Numerous moles by the patient's own estimate. Collected as part of a research study, without a referral diagnosis. A female subject aged 78. Dermoscopy of a skin lesion.
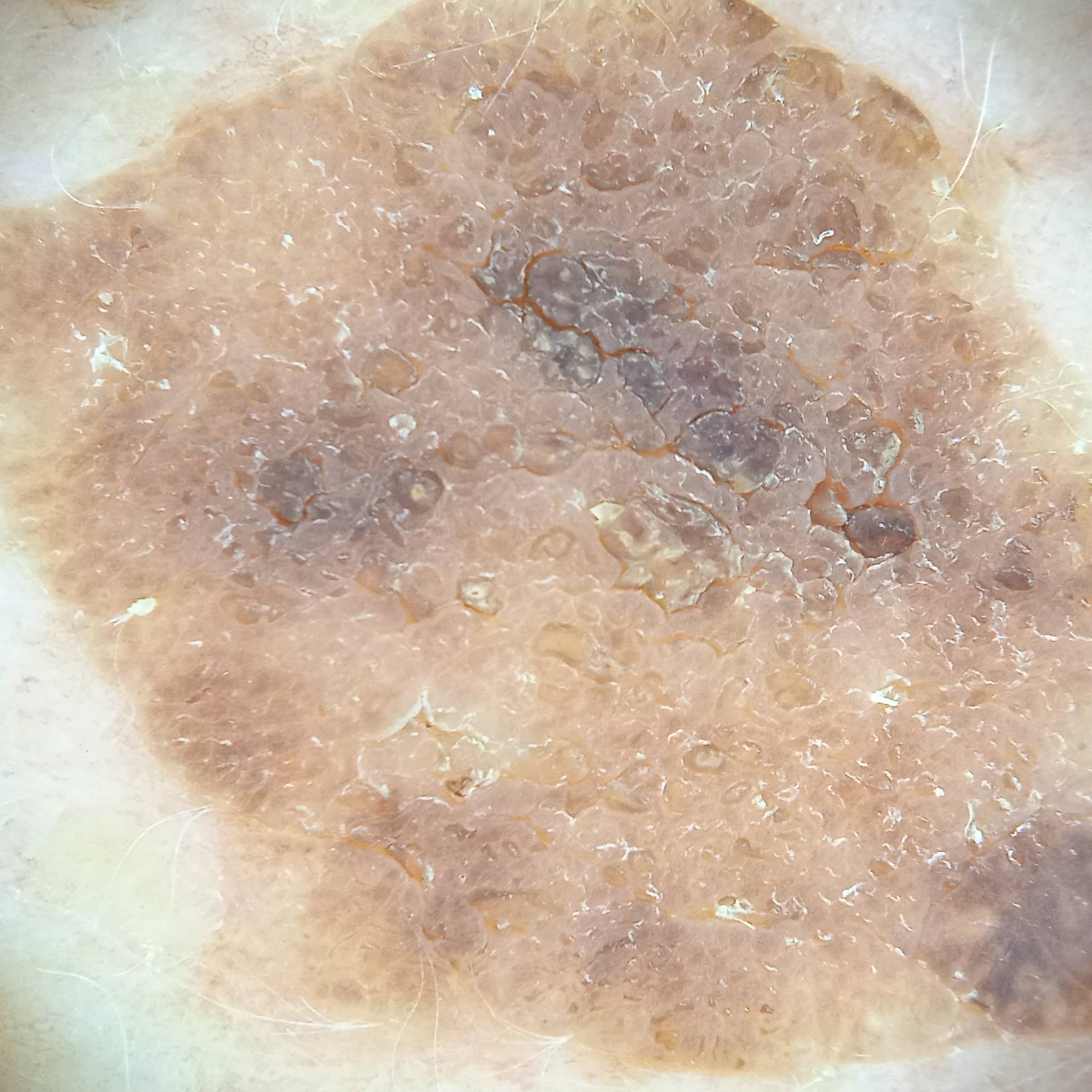The lesion involves the back. The lesion is about 15.7 mm across. Dermatologist review favored a seborrheic keratosis.